The patient says their skin reddens with sun exposure · by self-report, a personal history of cancer and a personal history of skin cancer · a clinical photograph showing a skin lesion · few moles overall by the patient's own estimate · a female subject aged 71.
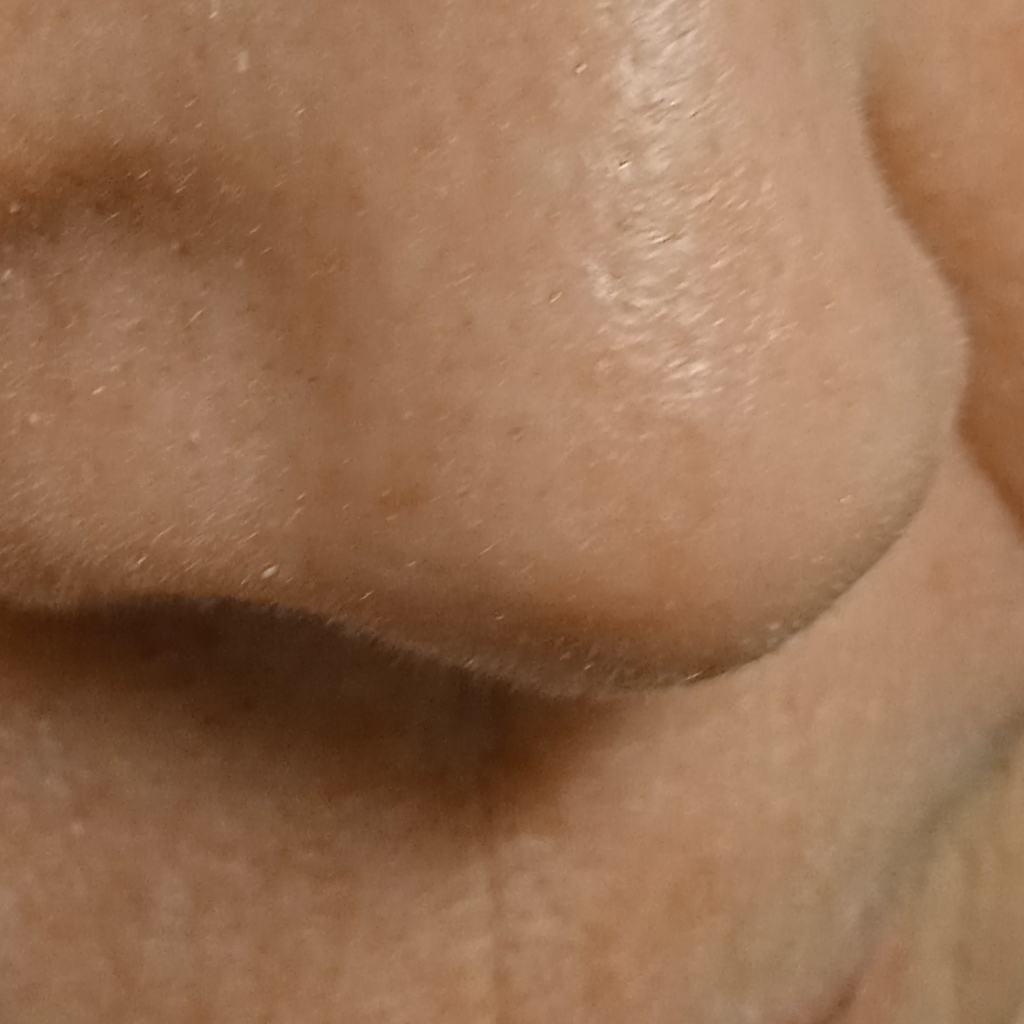Case:
* body site — the face
* diameter — 7.3 mm
* diagnostic label — actinic keratosis (dermatologist consensus)